A dermoscopic image of a skin lesion.
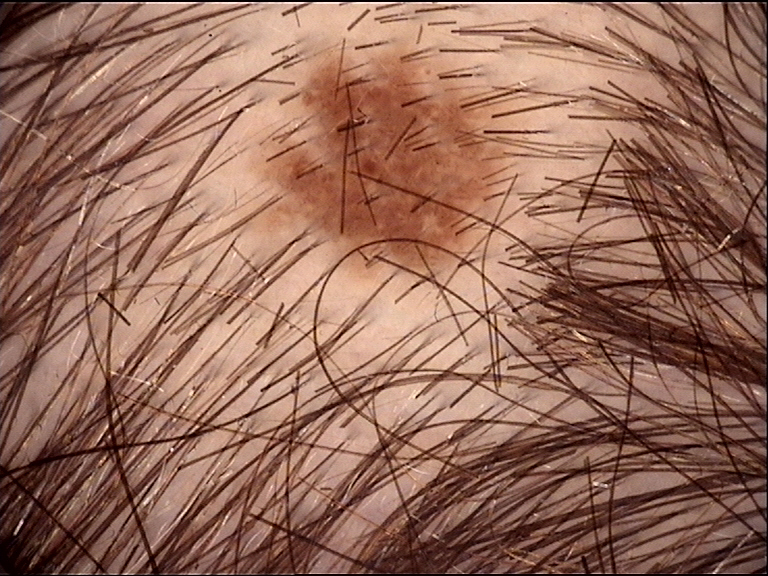Impression: Consistent with a dysplastic junctional nevus.